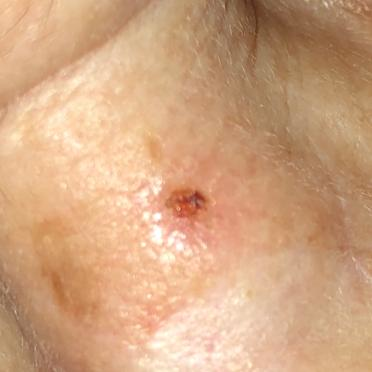patient = female, in their early 70s | Fitzpatrick = III | image type = clinical photo | exposure history = prior skin cancer (patient or family), prior malignancy (patient or family), no alcohol use | size = 4x3 mm | diagnostic label = basal cell carcinoma (biopsy-proven).